A skin lesion imaged with a dermatoscope:
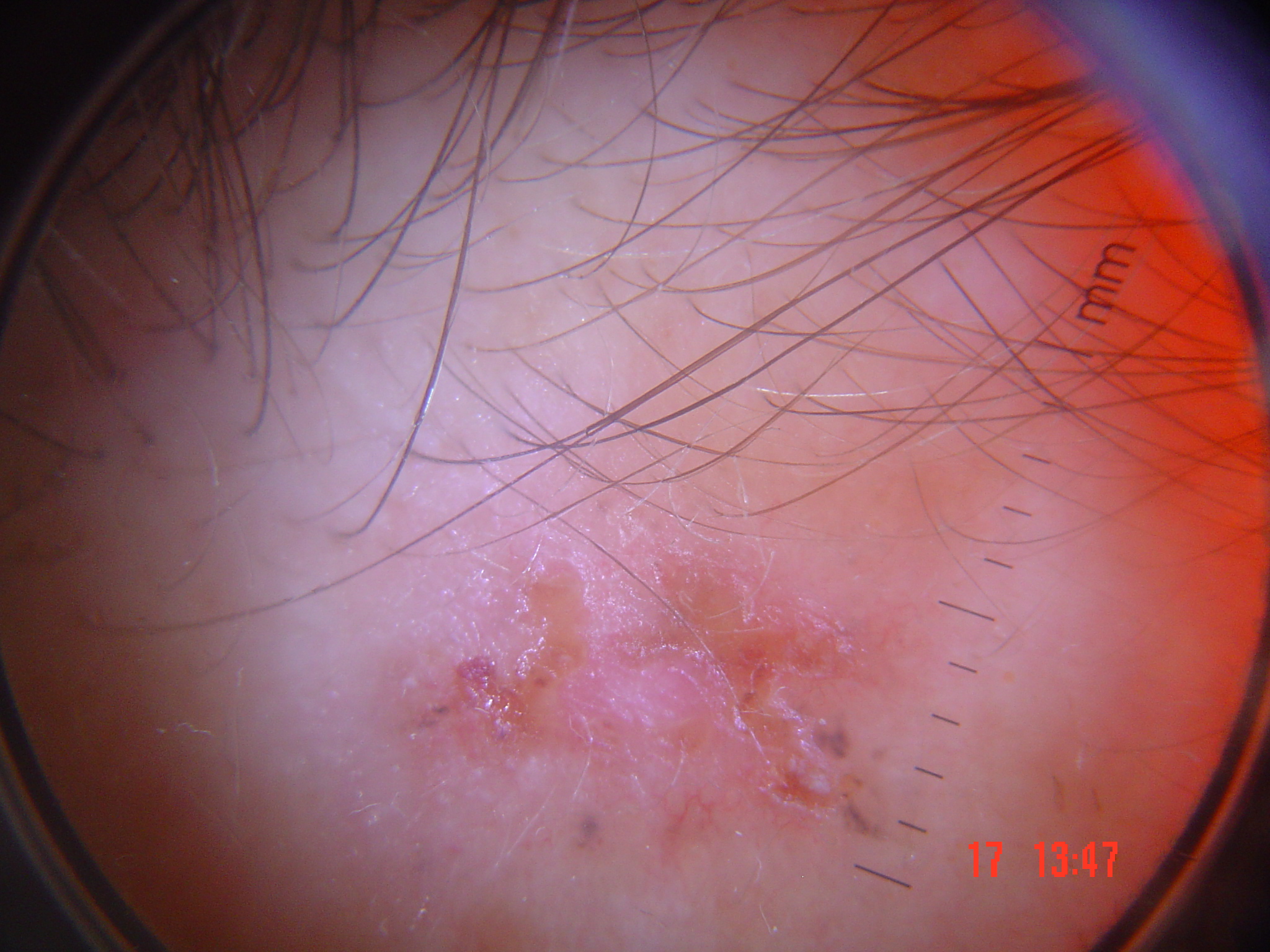The architecture is that of a keratinocytic lesion. Histopathology confirmed a basal cell carcinoma.